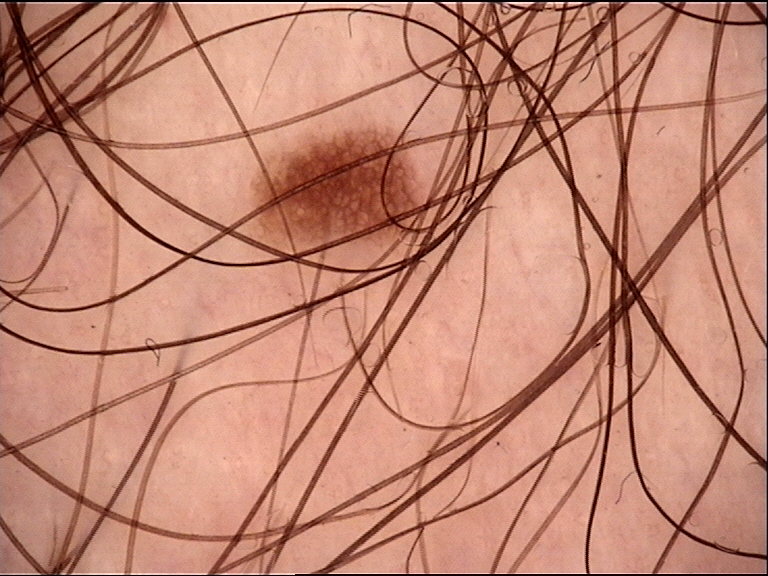Findings:
• diagnosis · dysplastic junctional nevus (expert consensus)